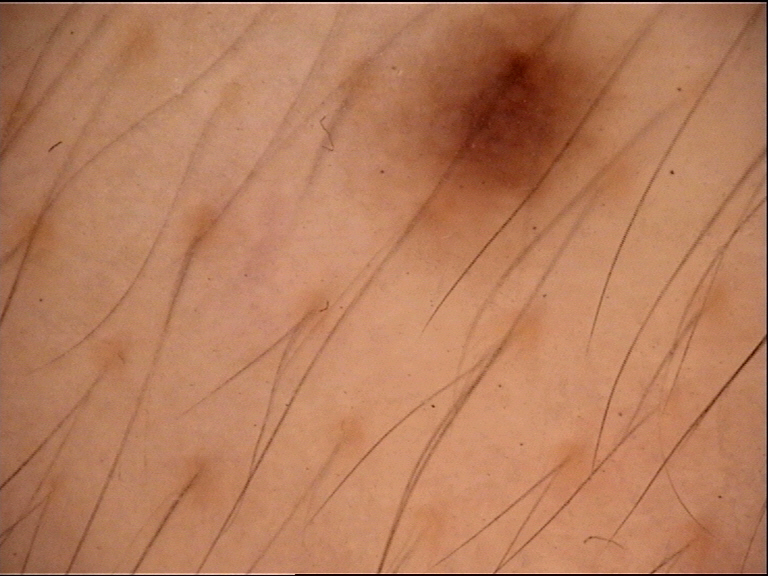A skin lesion imaged with a dermatoscope. The architecture is that of a banal lesion. The diagnostic label was a junctional nevus.